The affected area is the arm · the photo was captured at a distance: 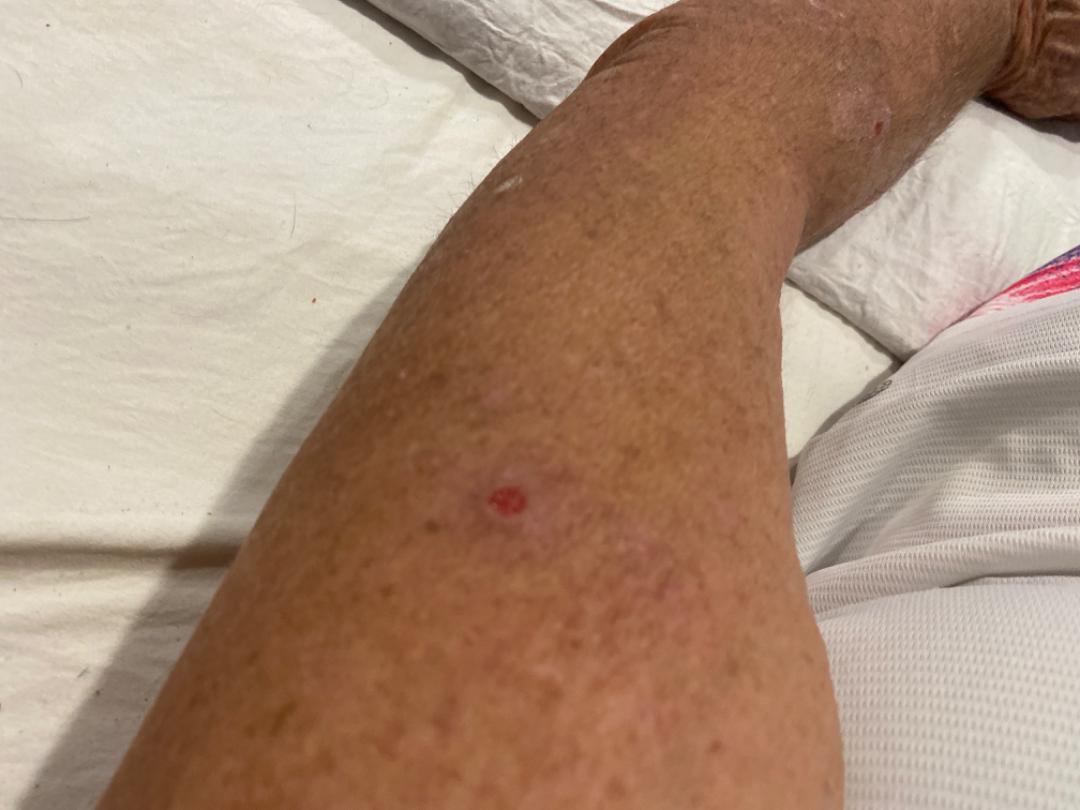assessment: ungradable on photographic review, associated systemic symptoms: none reported, history: one to four weeks, surface texture: rough or flaky and fluid-filled, symptoms: bothersome appearance.